A dermatoscopic image of a skin lesion.
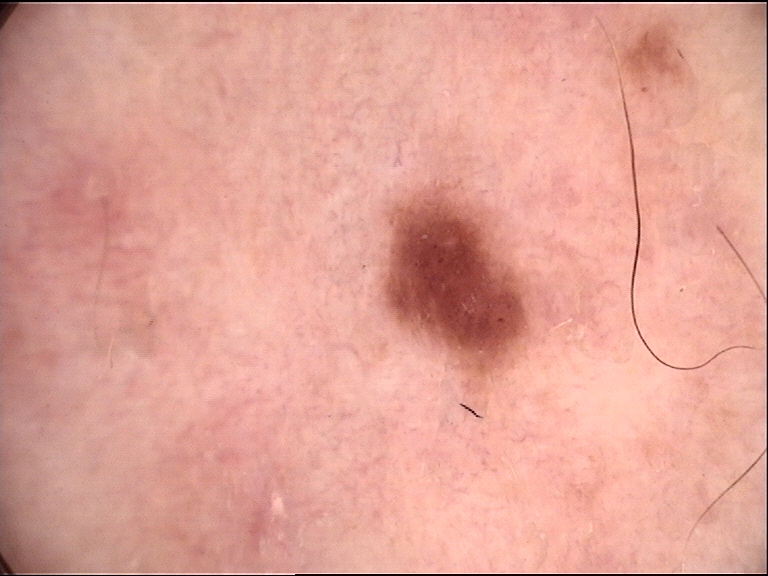Case:
– diagnosis: dysplastic junctional nevus (expert consensus)